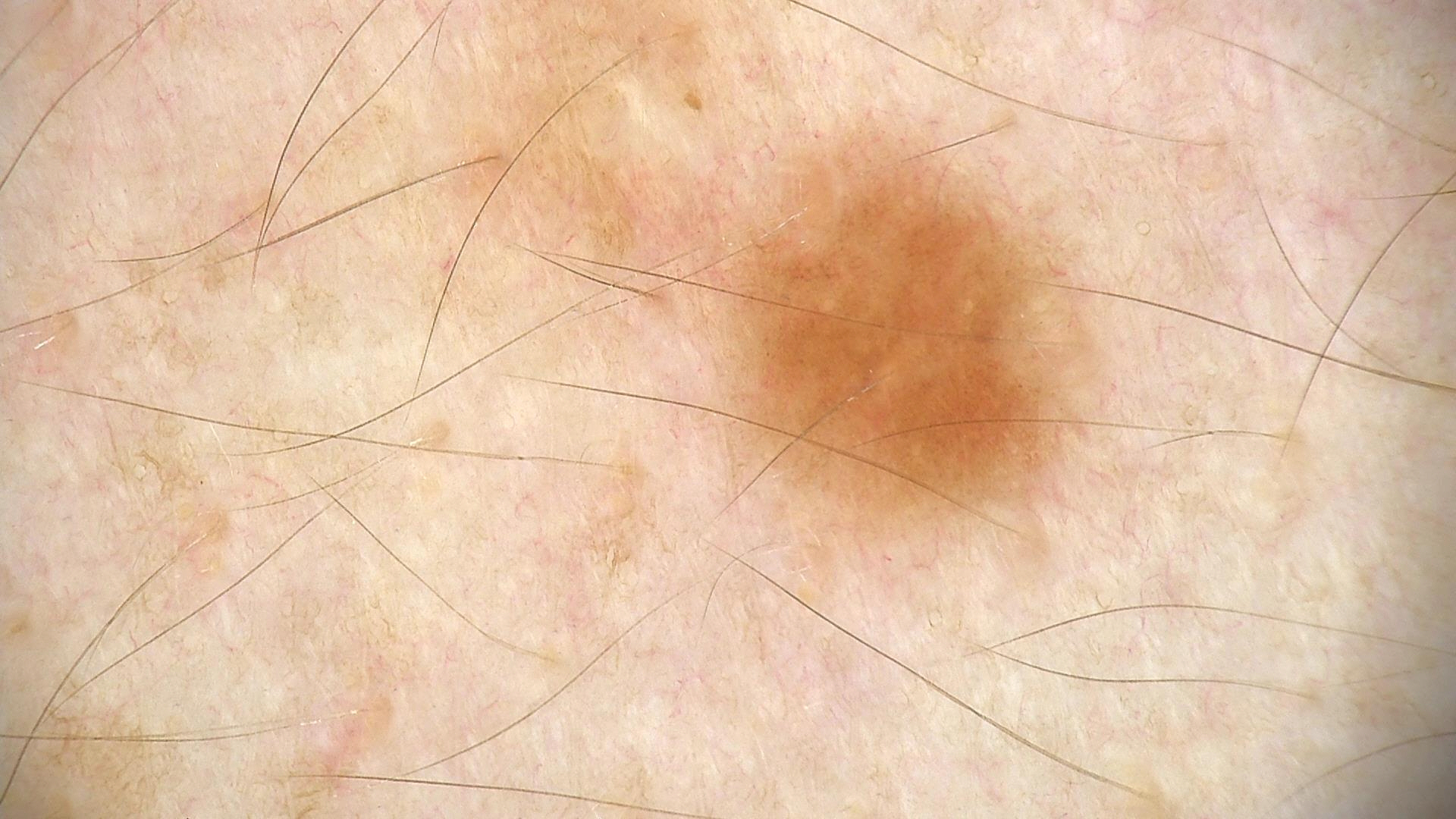– image — dermatoscopy
– class — dysplastic junctional nevus (expert consensus)